Skin tone: lay reviewers estimated 2 on the MST · close-up view.
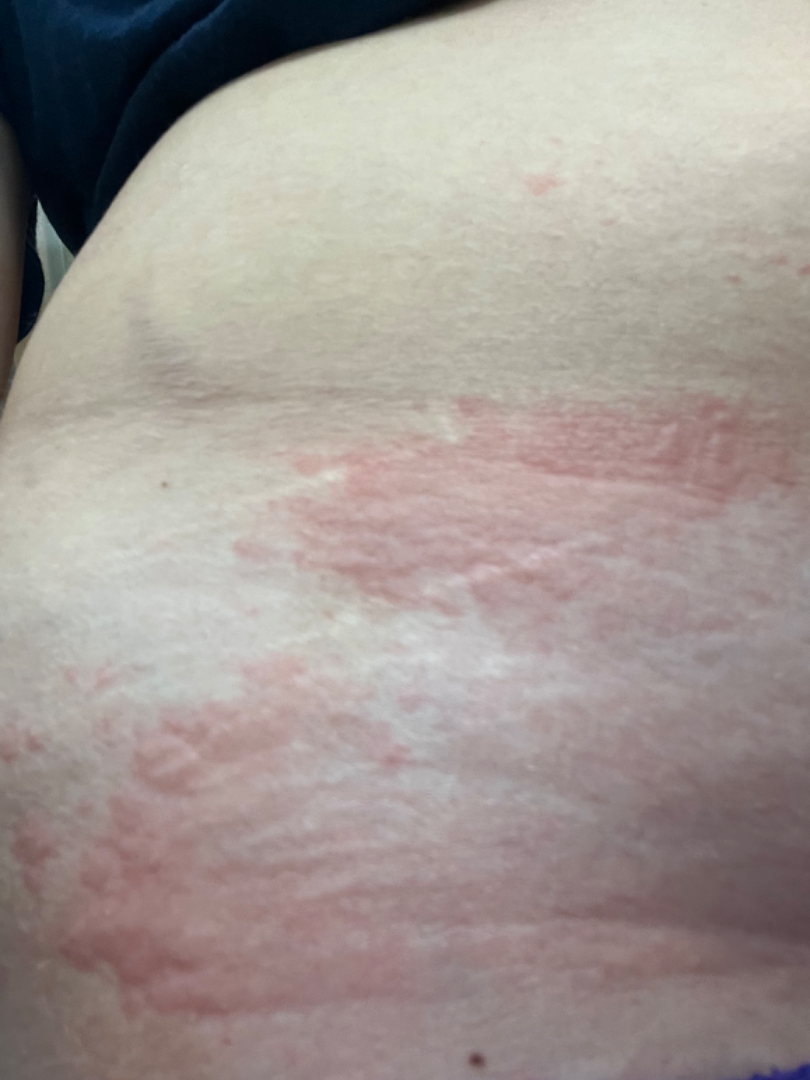The reviewing dermatologist was unable to assign a differential diagnosis from the image.